A dermoscopy image of a skin lesion · collected as part of a research study, without a referral diagnosis: 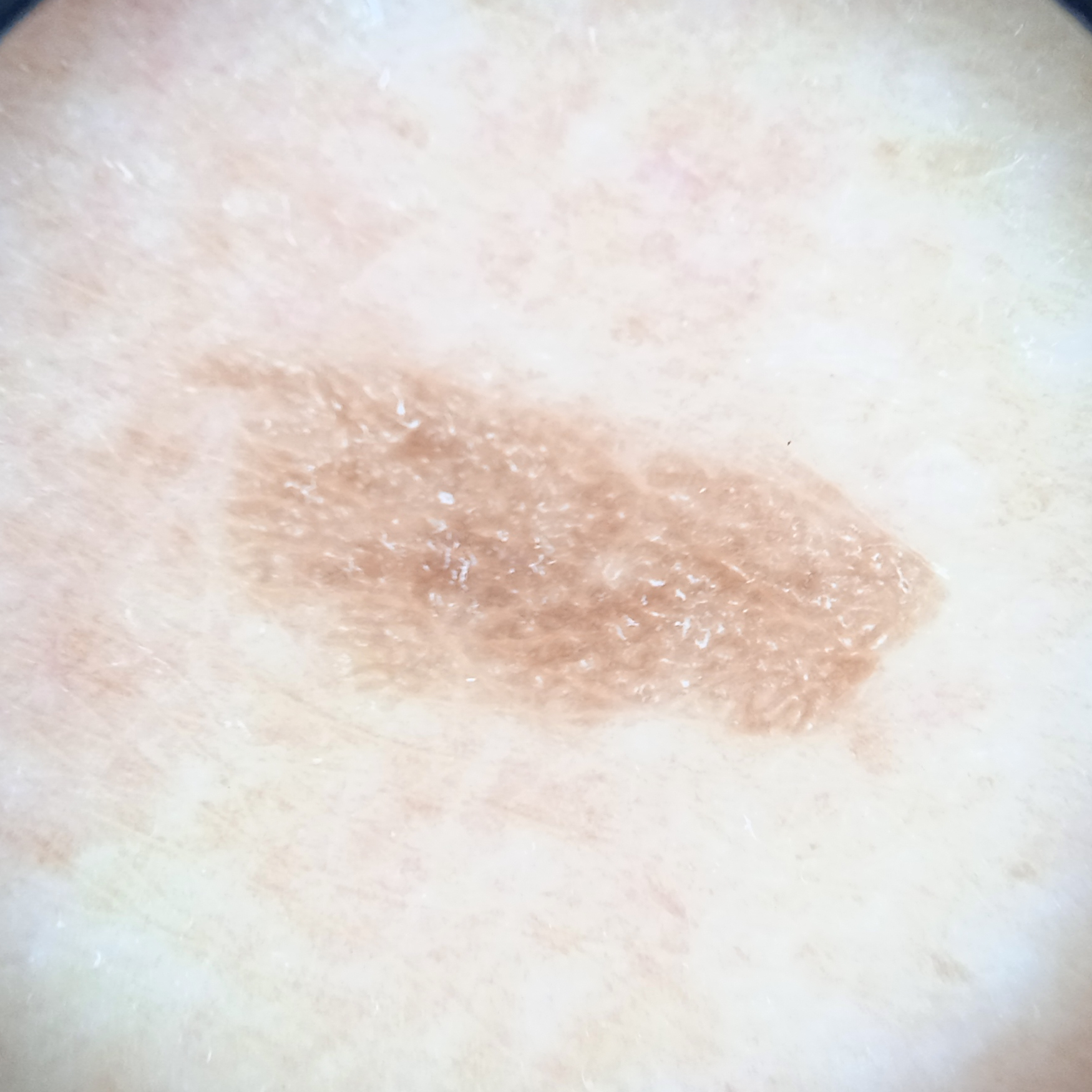site=the back; size=8.4 mm; assessment=seborrheic keratosis (dermatologist consensus).